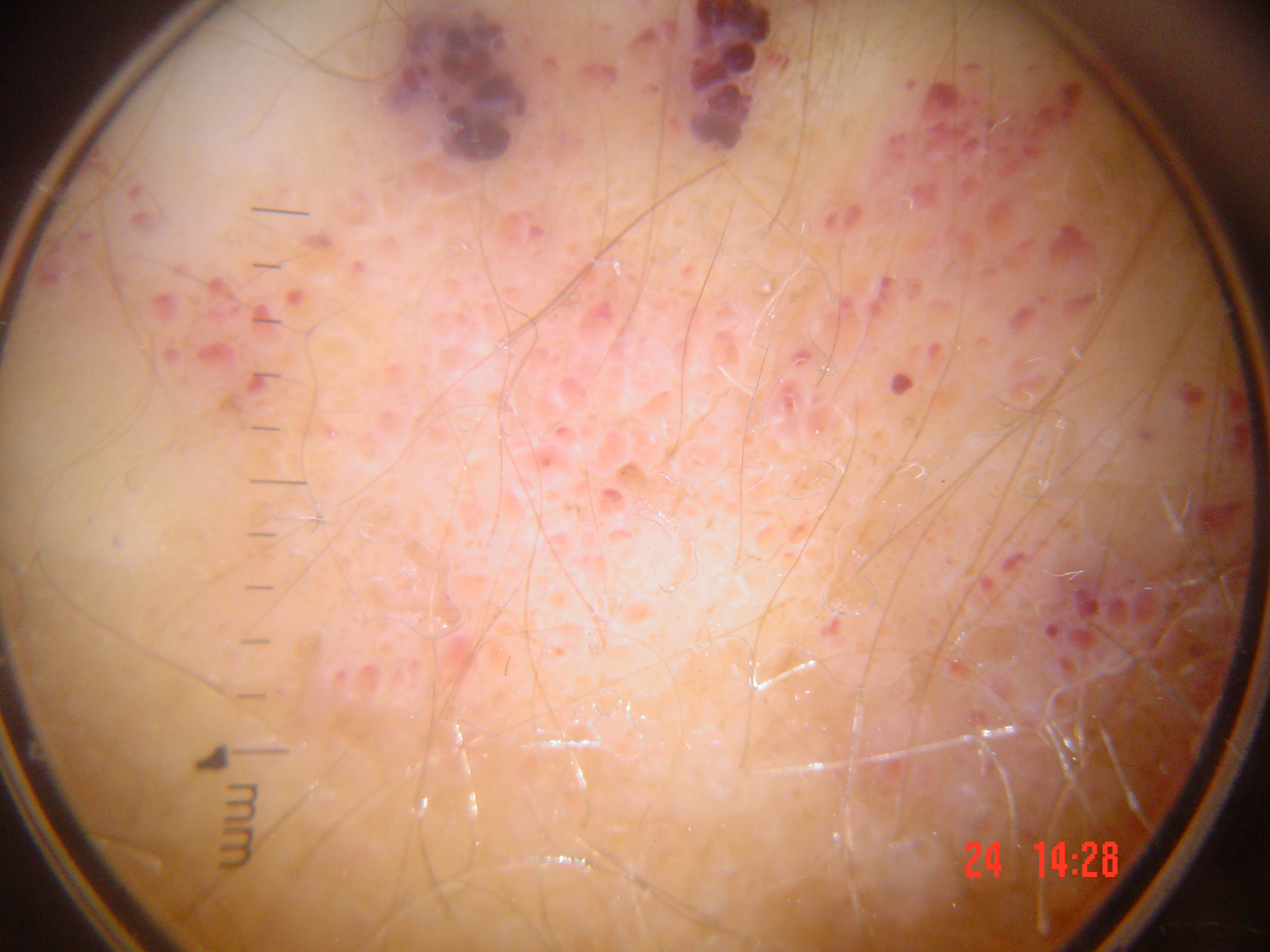<case>
<diagnosis>
<name>lymphangioma</name>
<code>la</code>
<malignancy>benign</malignancy>
<super_class>non-melanocytic</super_class>
<confirmation>expert consensus</confirmation>
</diagnosis>
</case>